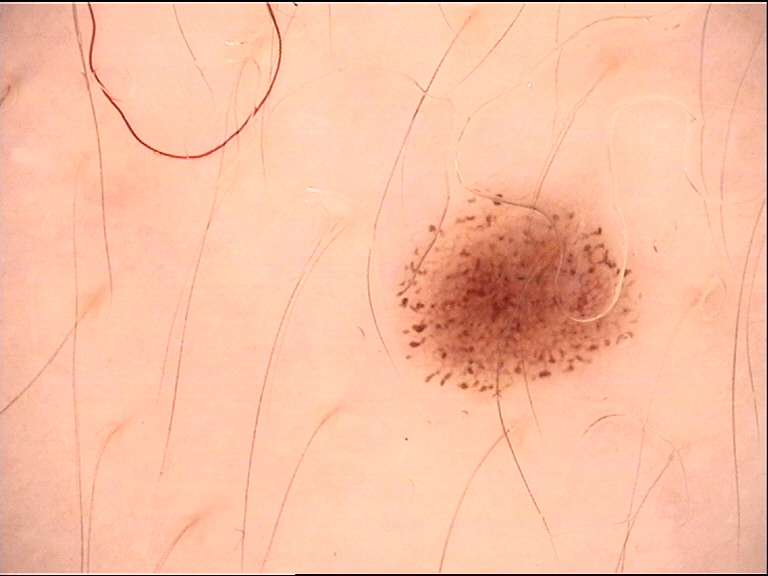image type: dermatoscopy, label: dysplastic junctional nevus (expert consensus).